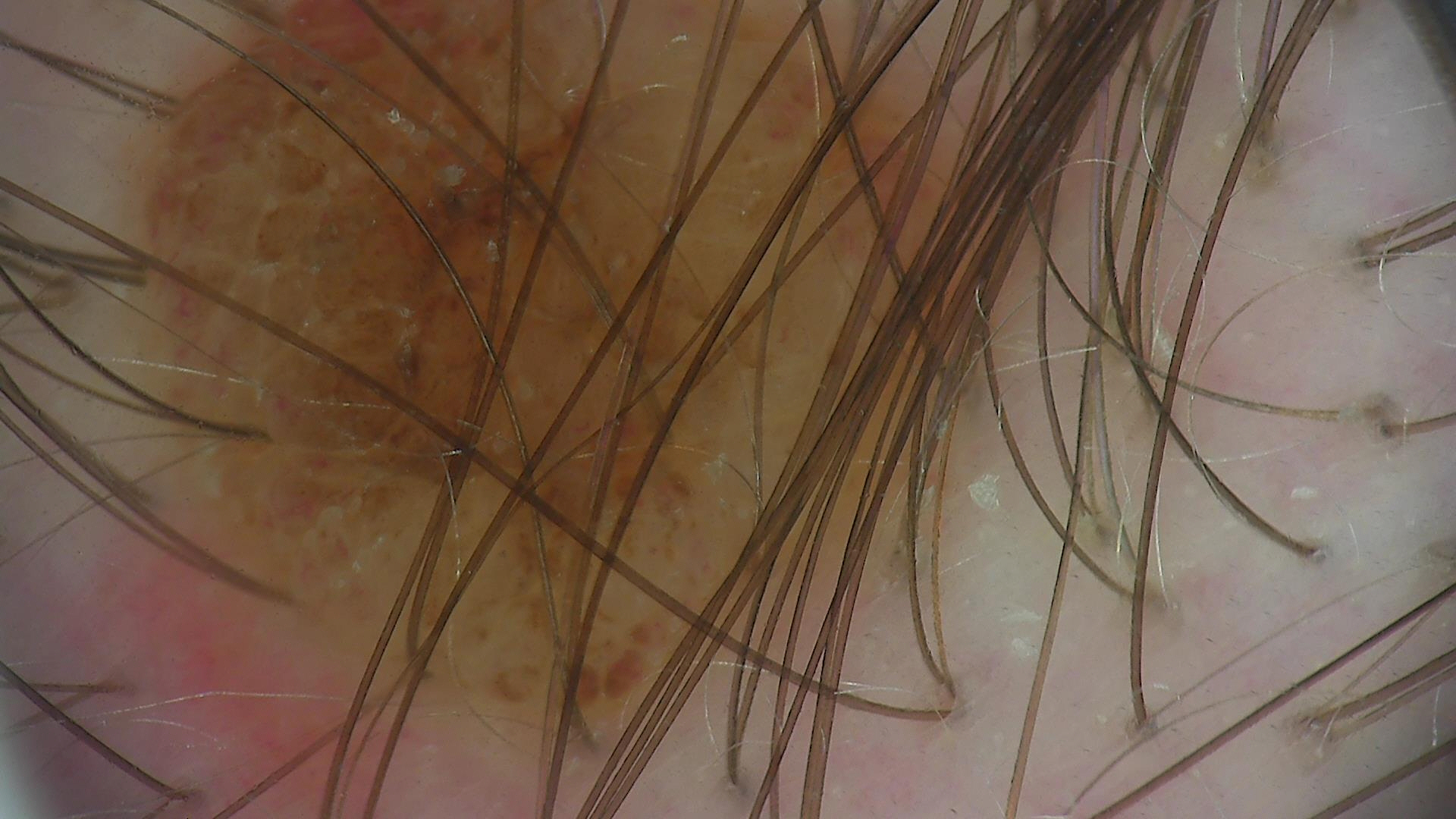image: dermoscopy
lesion_type:
  main_class: banal
  pattern: dermal
diagnosis:
  name: dermal nevus
  code: db
  malignancy: benign
  super_class: melanocytic
  confirmation: expert consensus